On a questionnaire the patient reported a personal history of cancer. A female subject aged 84. The patient says their skin tans without first burning:
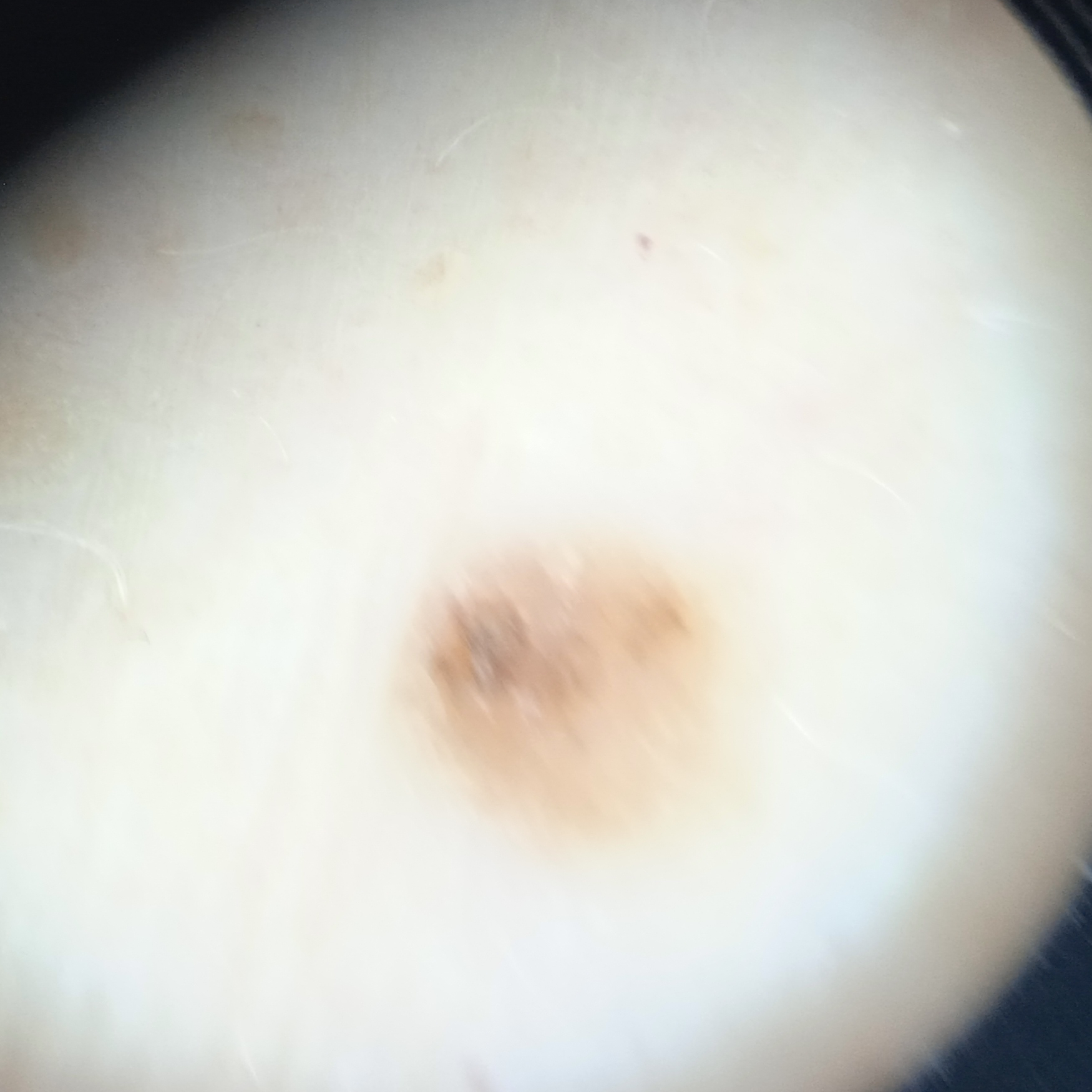The lesion was assessed as a seborrheic keratosis.